A dermoscopy image of a single skin lesion: 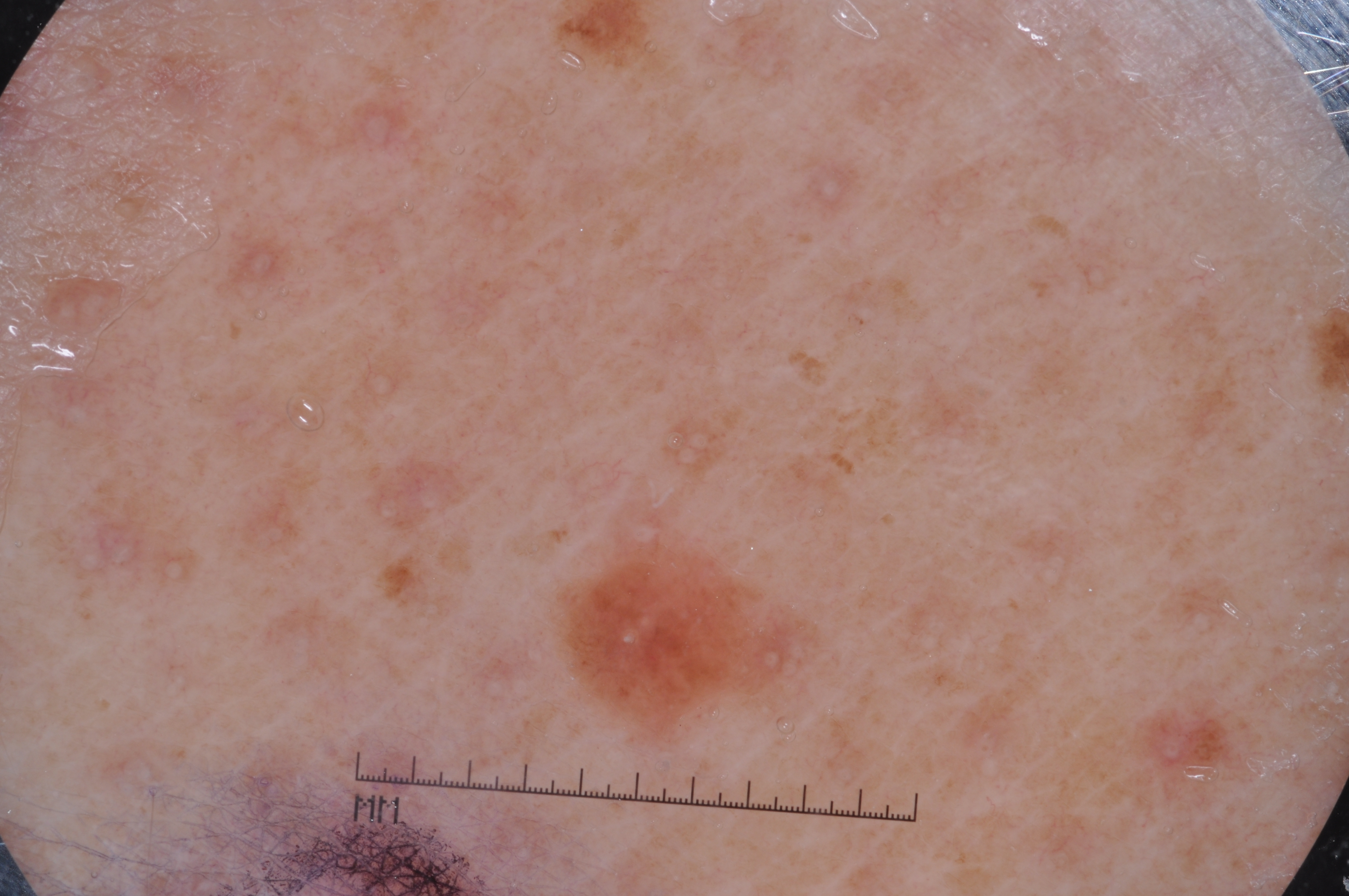Image and clinical context:
With coordinates (x1, y1, x2, y2), the lesion is located at [549,499,829,751]. The lesion covers approximately 3% of the dermoscopic field. The dermoscopic pattern shows milia-like cysts.
Impression:
Diagnosed as a melanocytic nevus, a benign skin lesion.